A dermoscopic close-up of a skin lesion.
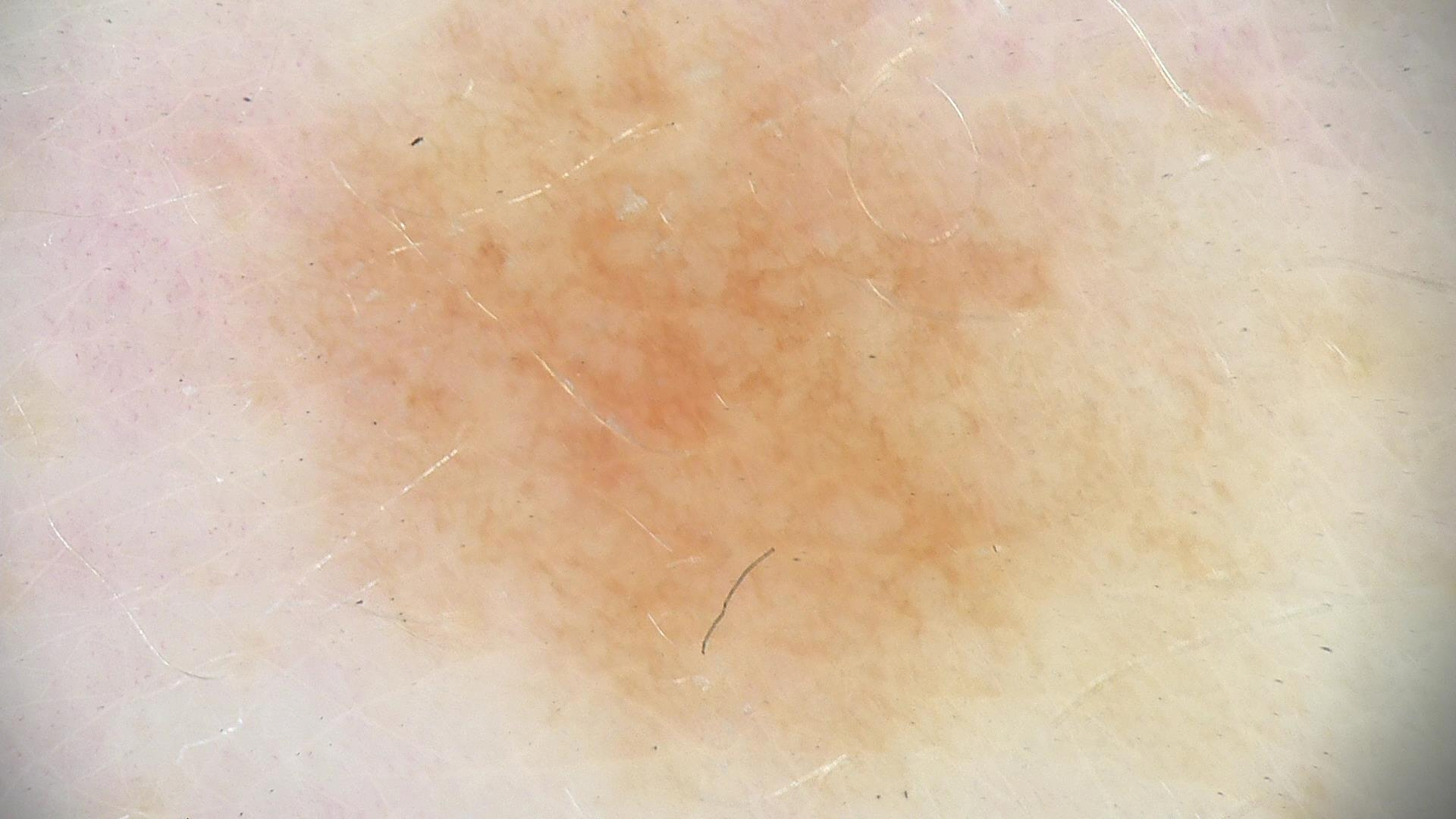Case:
– diagnosis · dysplastic junctional nevus (expert consensus)